Human graders estimated a Monk skin tone scale of 2. The photograph is a close-up of the affected area. The patient notes the lesion is raised or bumpy. Reported lesion symptoms include burning and itching. The condition has been present for less than one week.
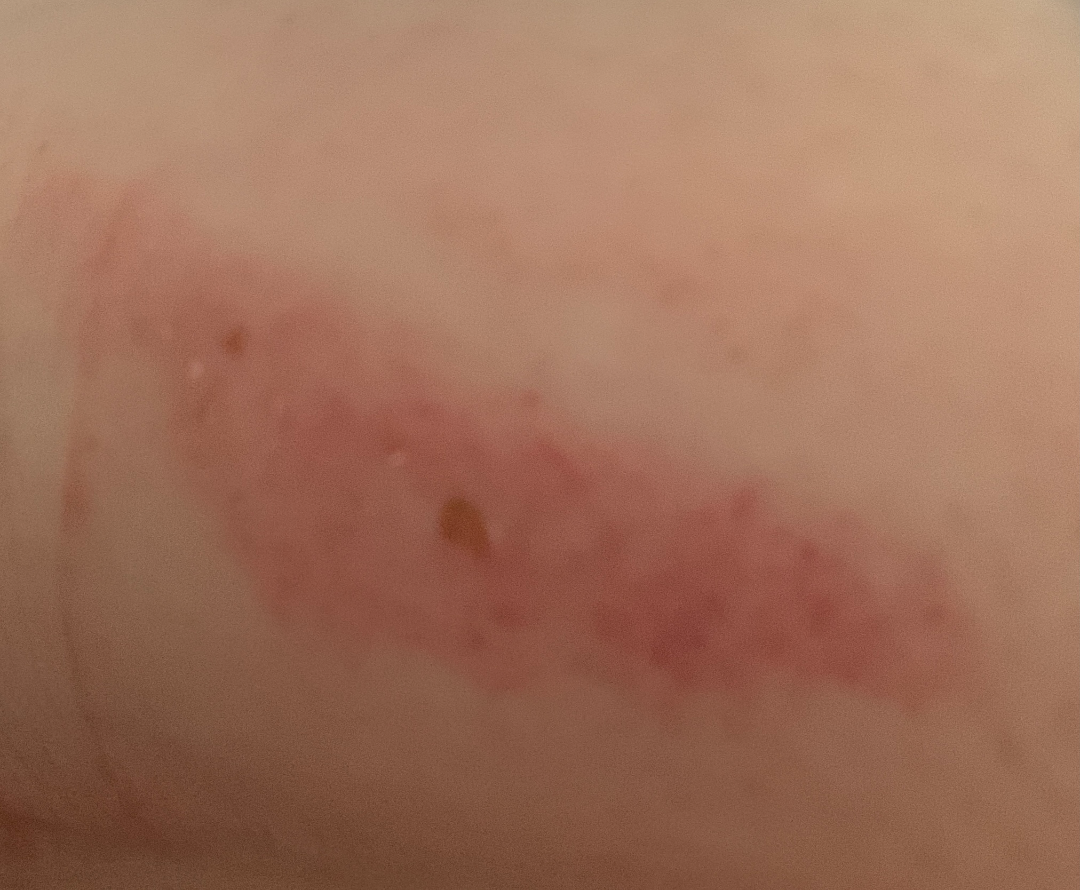{"assessment": "unable to determine"}